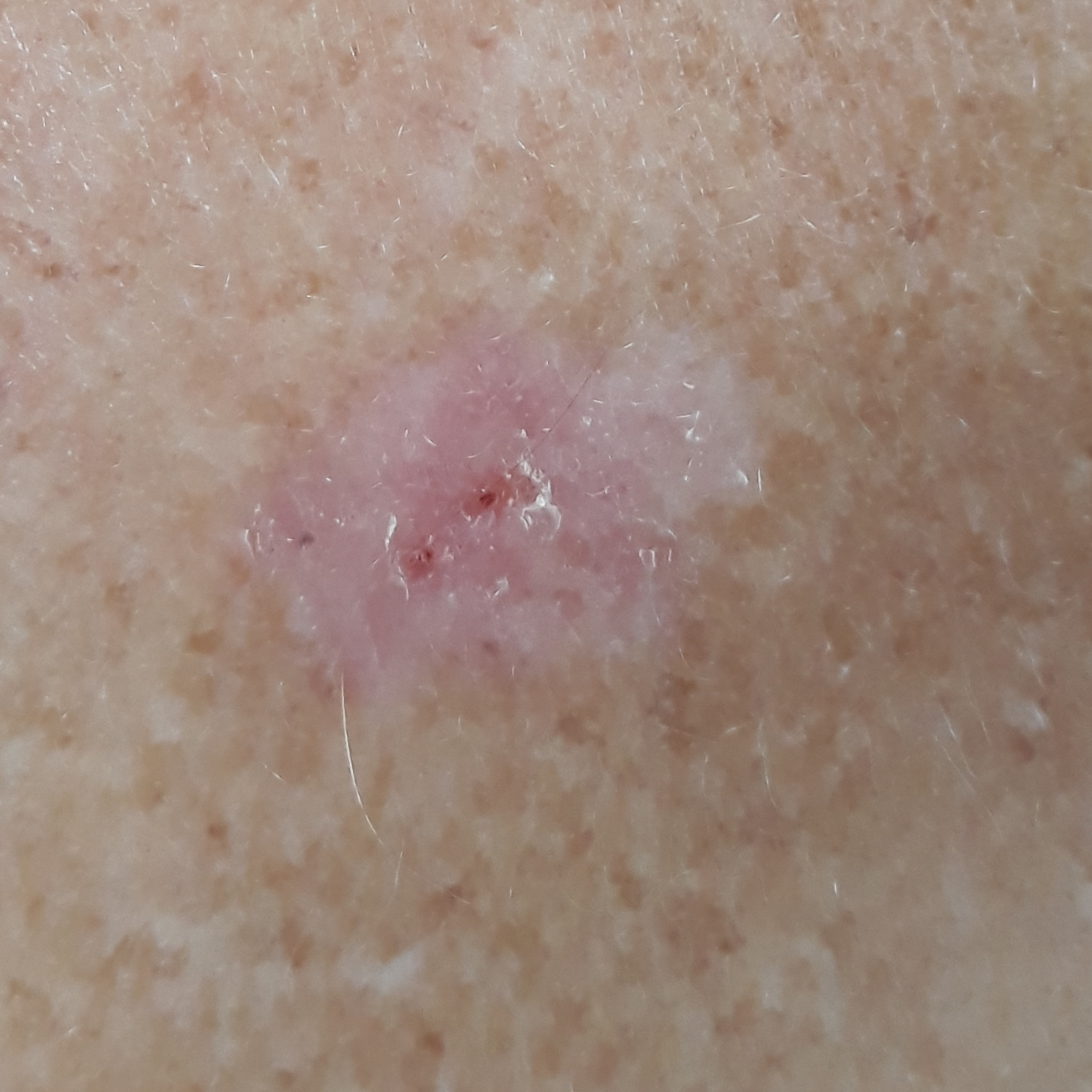The patient was assessed as Fitzpatrick skin type II. A male patient in their 50s. History notes pesticide exposure, prior malignancy (patient or family), and alcohol use. The lesion is located on the back. The lesion measures 7 × 5 mm. The patient reports that the lesion itches, but is not elevated. Consistent with an actinic keratosis.